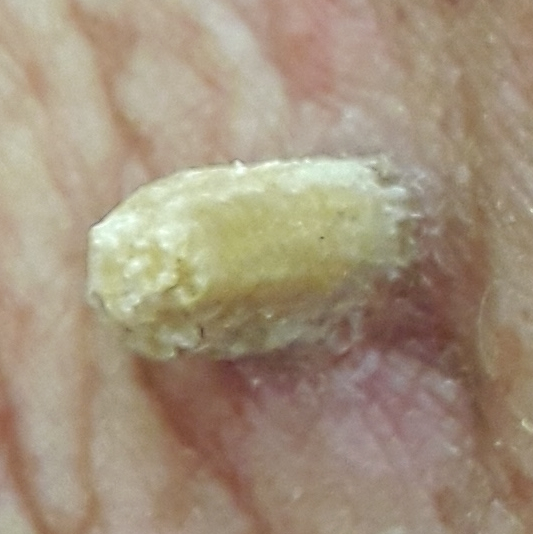Diagnosis:
Histopathologically confirmed as an actinic keratosis.